Dermoscopy of a skin lesion: 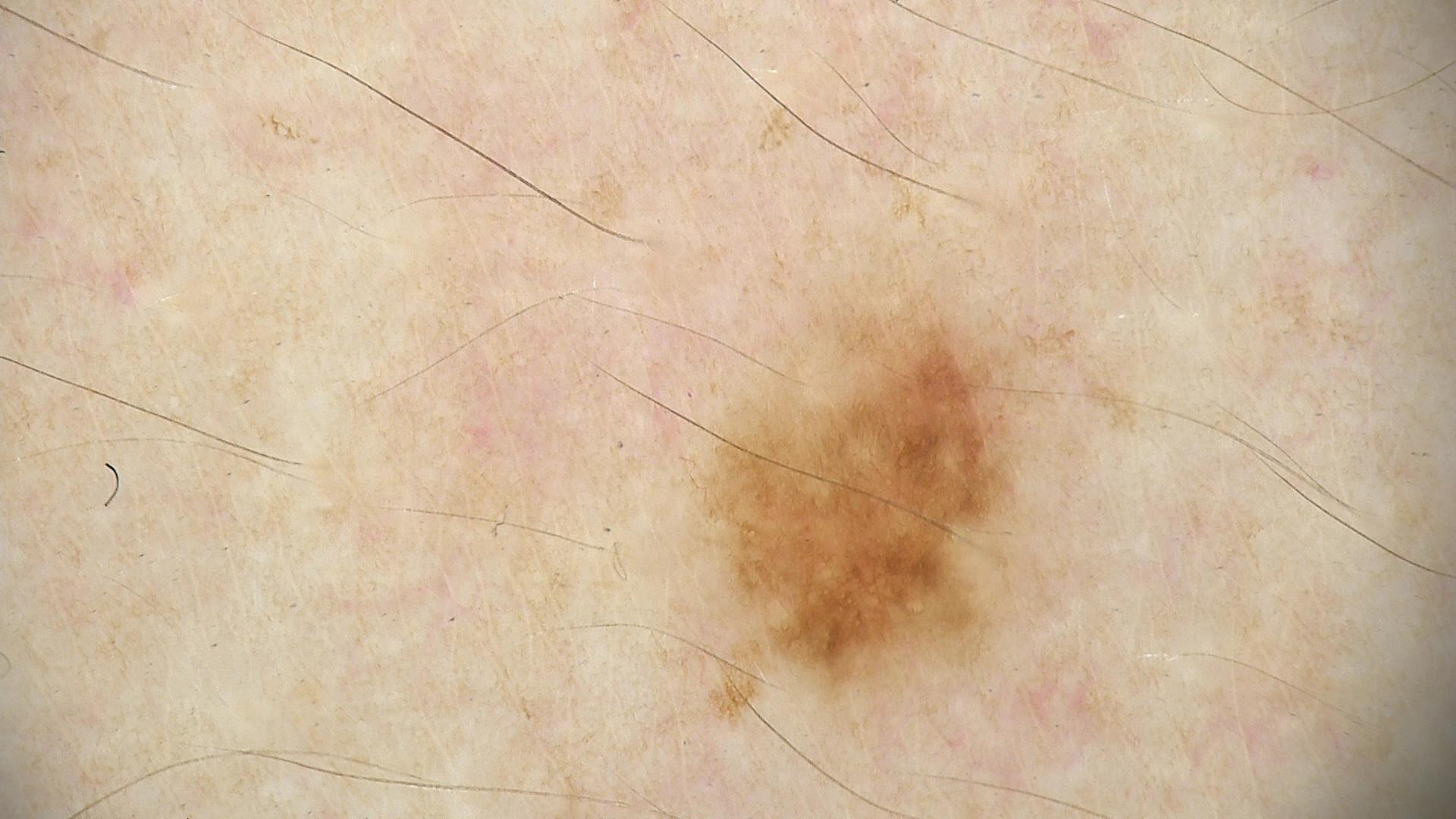diagnosis:
  name: dysplastic junctional nevus
  code: jd
  malignancy: benign
  super_class: melanocytic
  confirmation: expert consensus